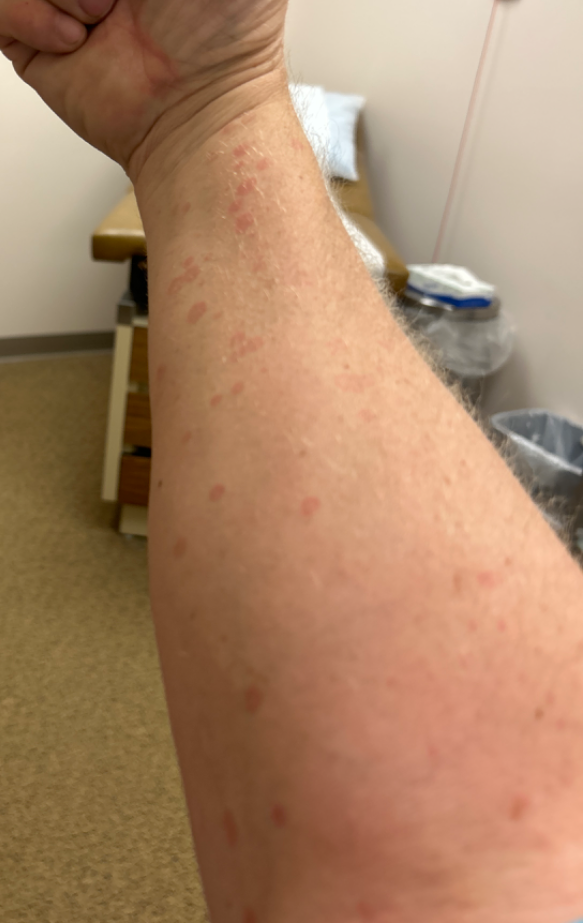Patient information:
The patient notes the lesion is flat. The photograph was taken at a distance.
Review:
In keeping with Tinea Versicolor.